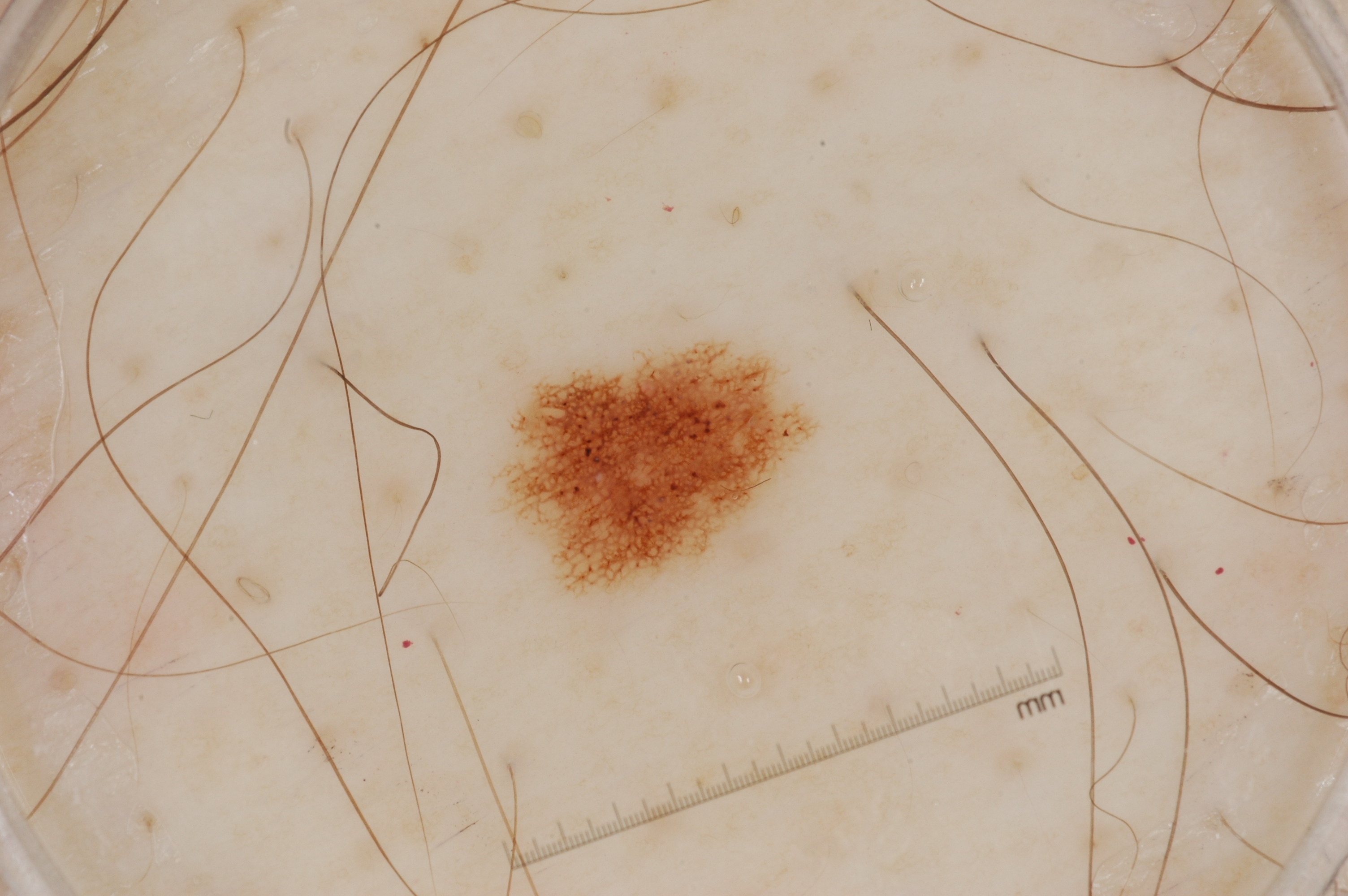The subject is a male in their mid-40s.
A dermoscopic close-up of a skin lesion.
A small lesion within a wider field of skin.
Dermoscopic assessment notes pigment network; no milia-like cysts, streaks, or negative network.
The lesion's extent is x1=516, y1=343, x2=801, y2=588.
Clinically diagnosed as a melanocytic nevus.